This image was taken at a distance.
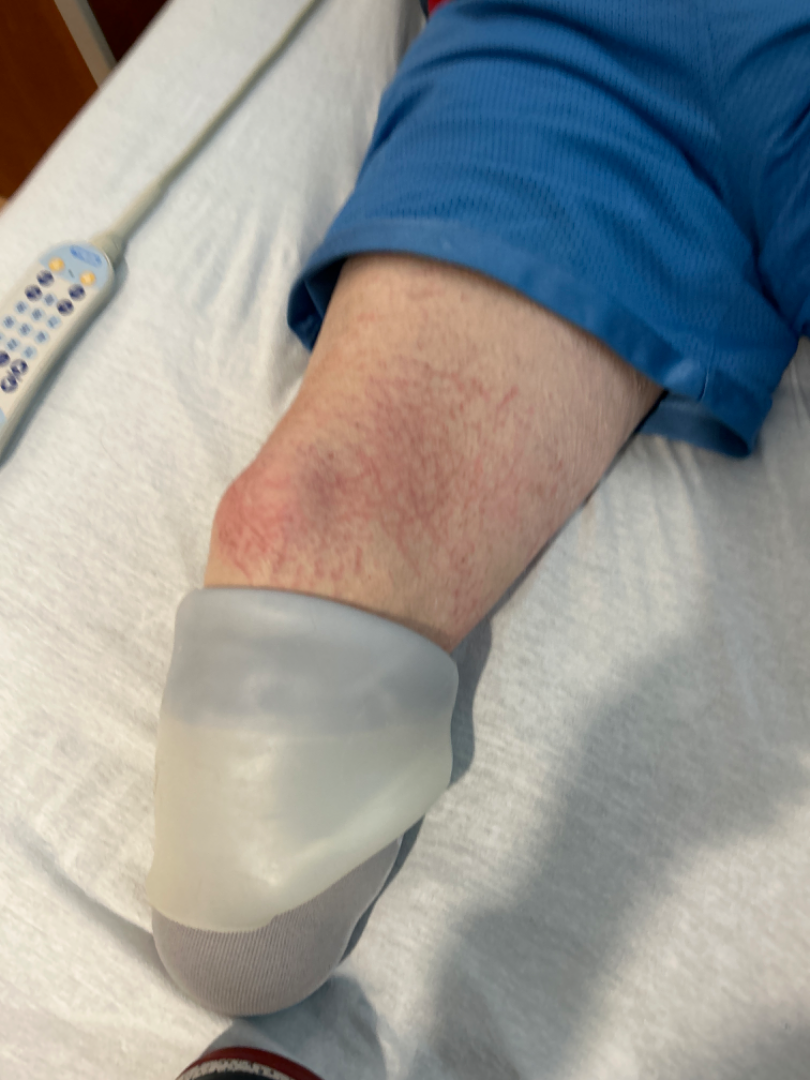Notes:
– differential diagnosis: consistent with Eczema